The photograph is a close-up of the affected area:
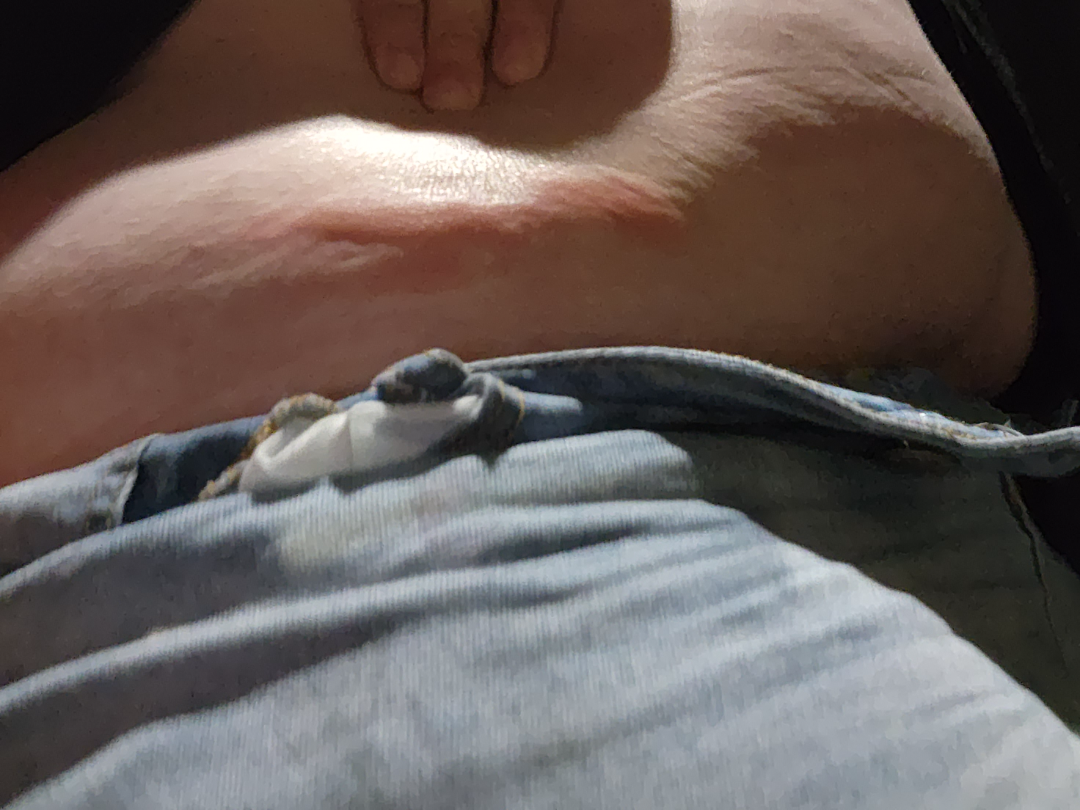The skin findings could not be characterized from the image.